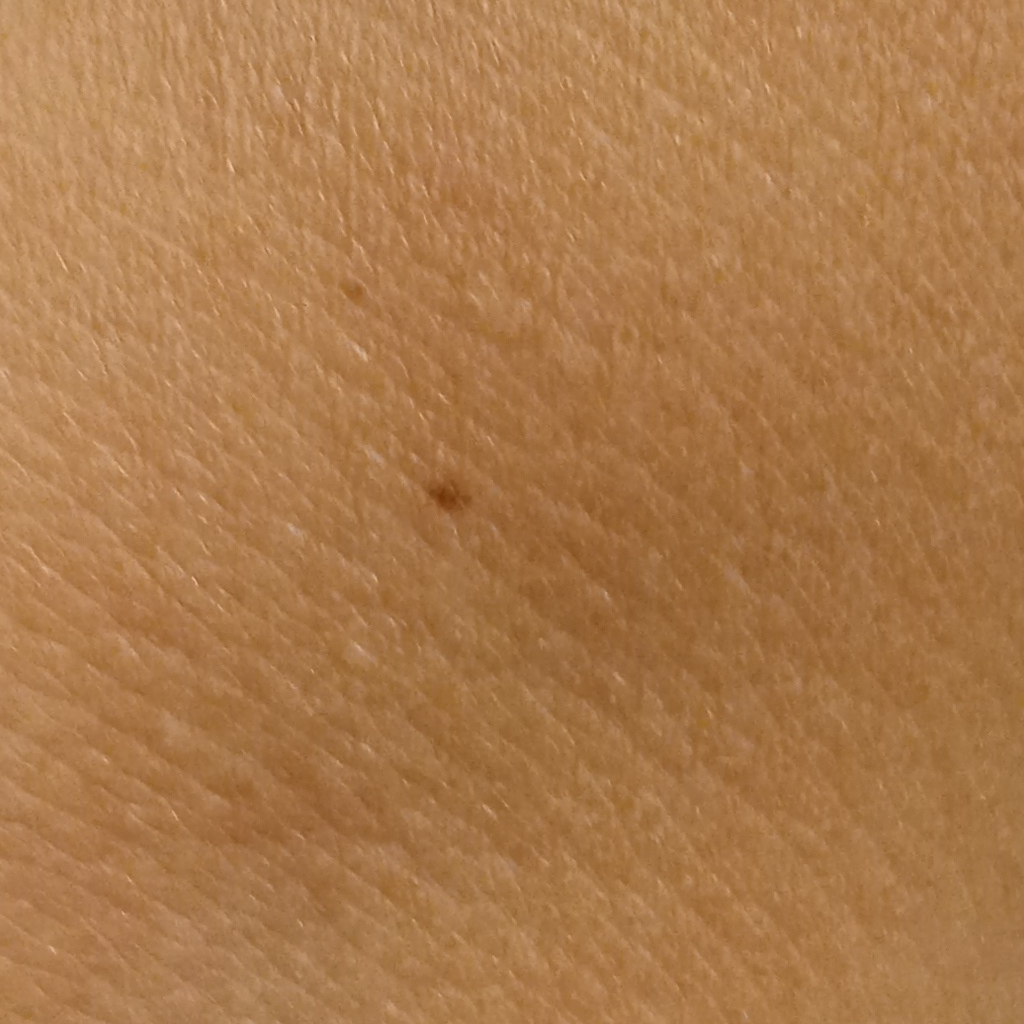Collected as part of a research study, without a referral diagnosis.
A macroscopic clinical photograph of a skin lesion.
The lesion is on an arm.
The lesion is about 1.9 mm across.
The lesion was assessed as a melanocytic nevus.